An overview clinical photograph of a skin lesion:
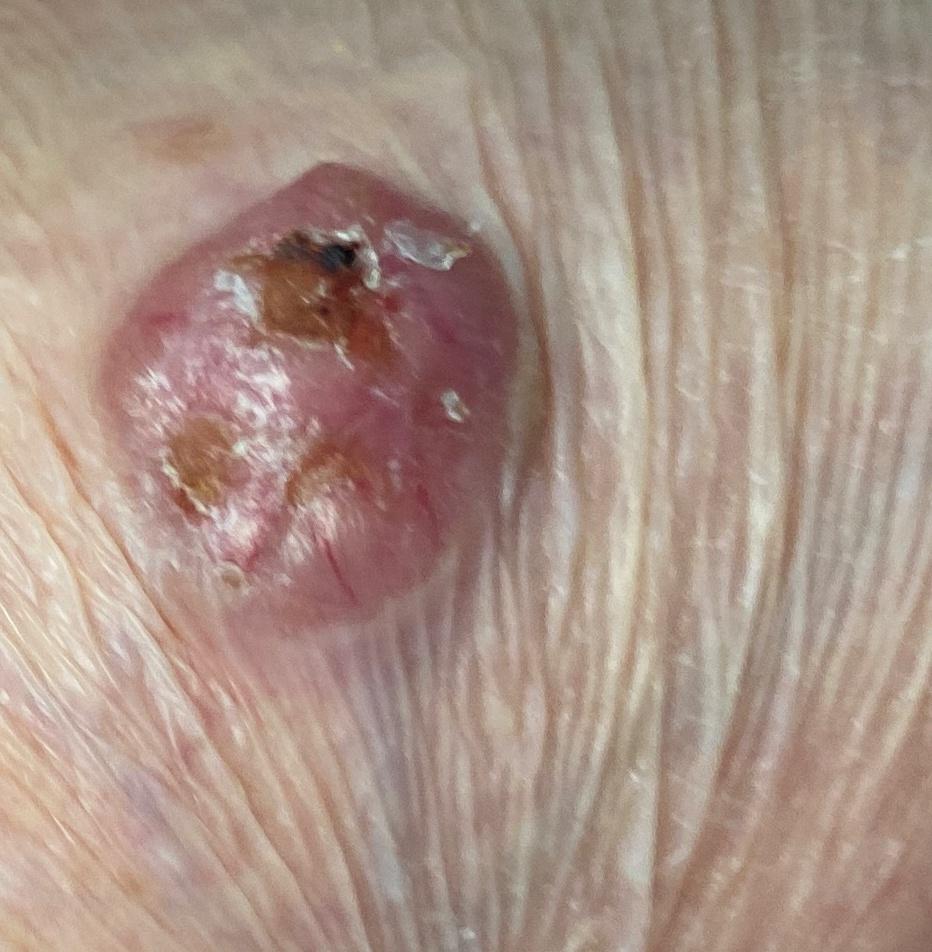Findings:
* body site: an upper extremity
* diagnosis: Basal cell carcinoma (biopsy-proven)